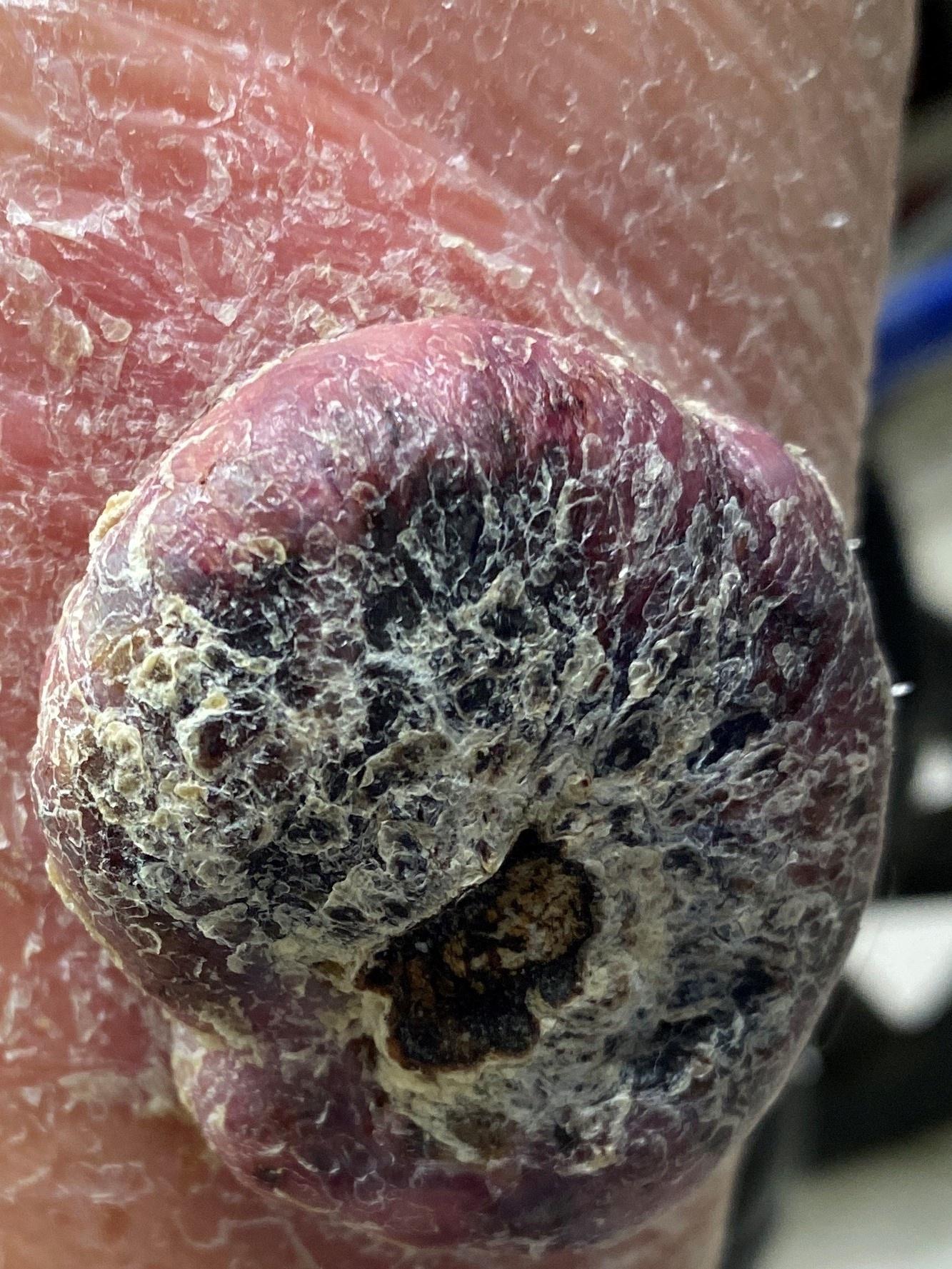<lesion>
  <skin_type>II</skin_type>
  <image>clinical photograph</image>
  <lesion_location>
    <region>a lower extremity</region>
  </lesion_location>
  <diagnosis>
    <name>Squamous cell carcinoma</name>
    <malignancy>malignant</malignancy>
    <confirmation>histopathology</confirmation>
    <lineage>epidermal</lineage>
  </diagnosis>
</lesion>